A skin lesion imaged with a dermatoscope.
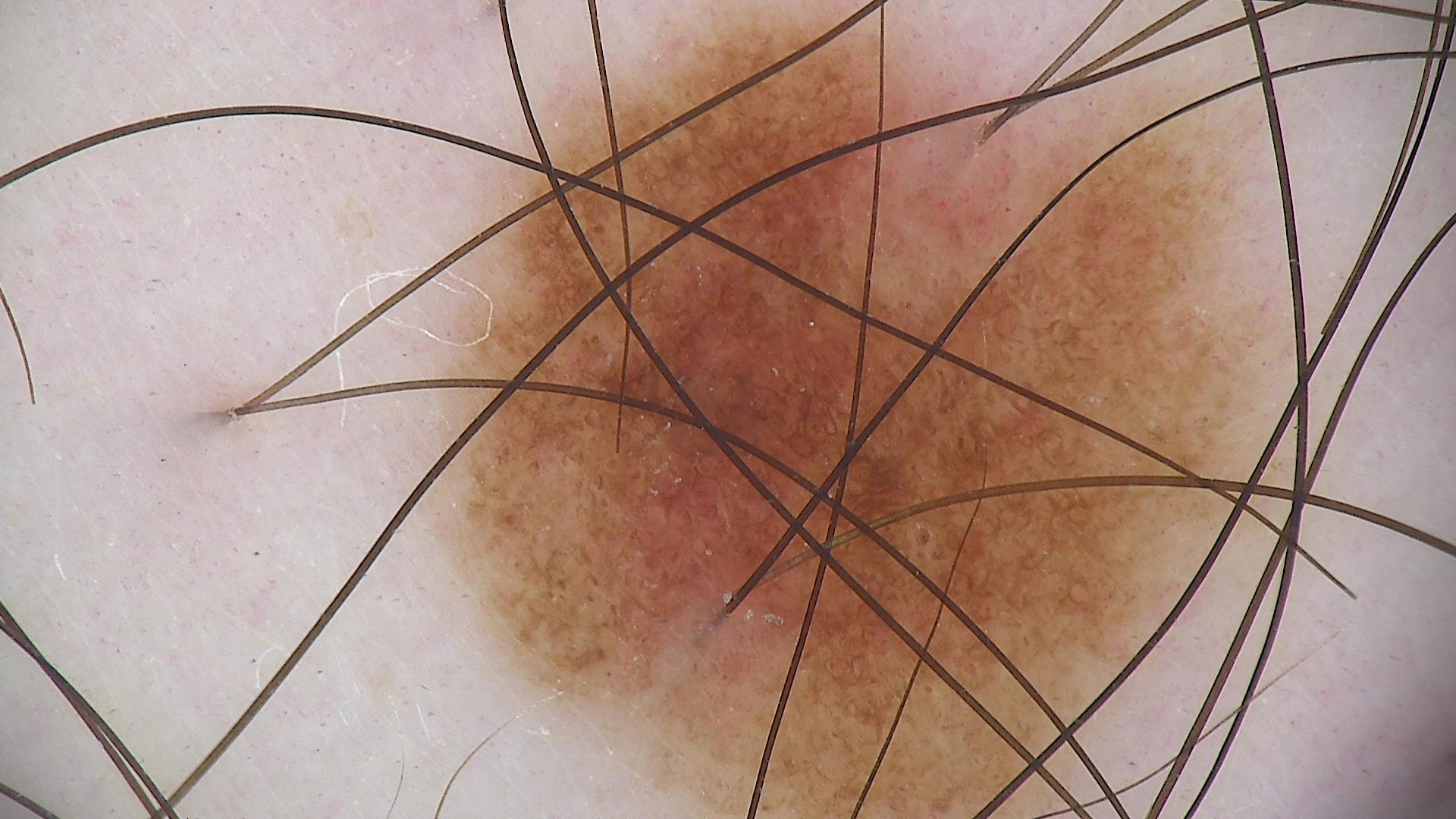Conclusion:
Labeled as a dysplastic junctional nevus.